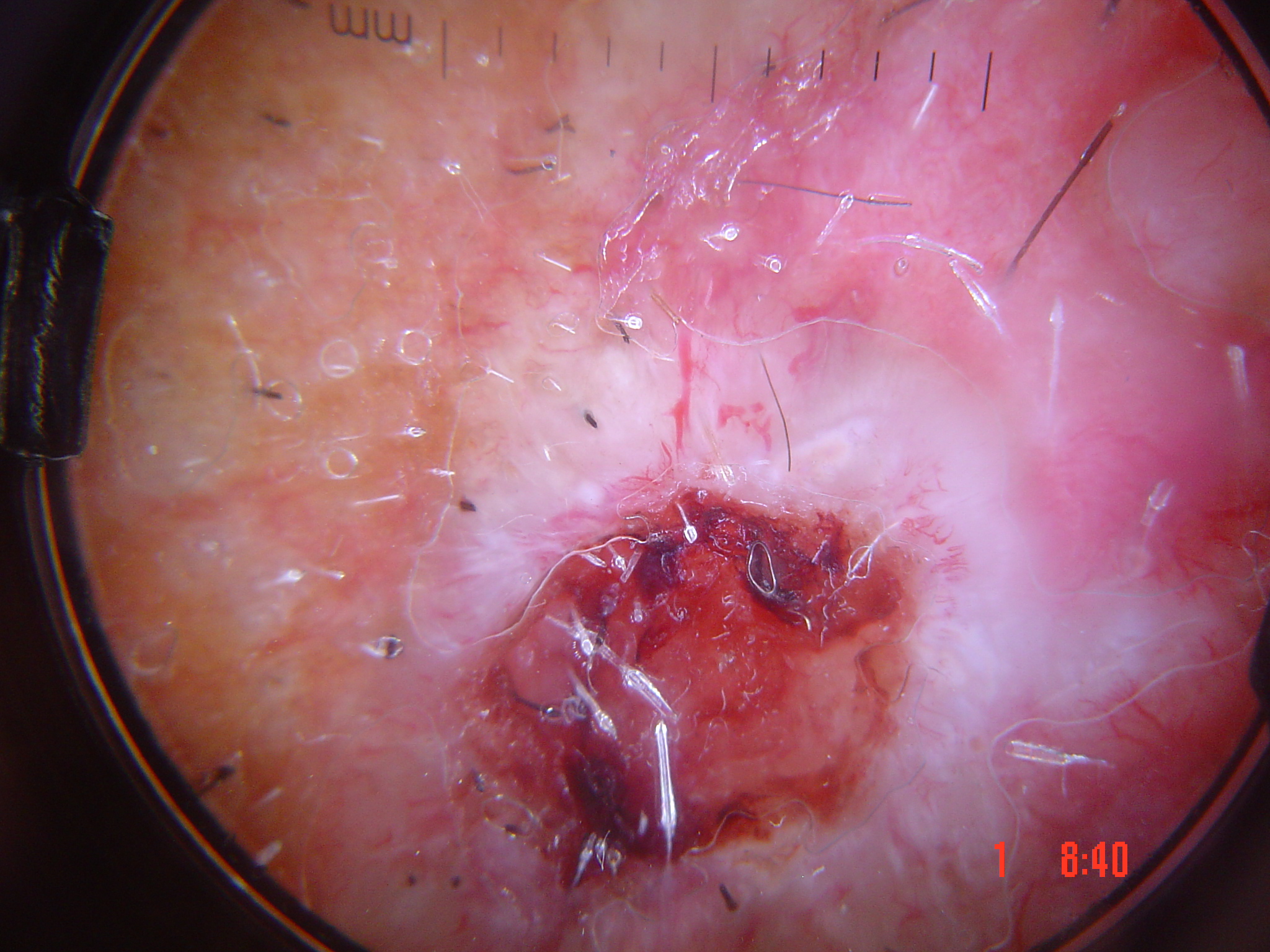Case: A dermatoscopic image of a skin lesion. This is a keratinocytic lesion. Conclusion: Histopathologically confirmed as a basal cell carcinoma.